Female subject, age 50–59; texture is reported as raised or bumpy and fluid-filled; the patient considered this skin that appeared healthy to them; the patient reports itching; an image taken at a distance; the back of the hand is involved; the condition has been present for less than one week.
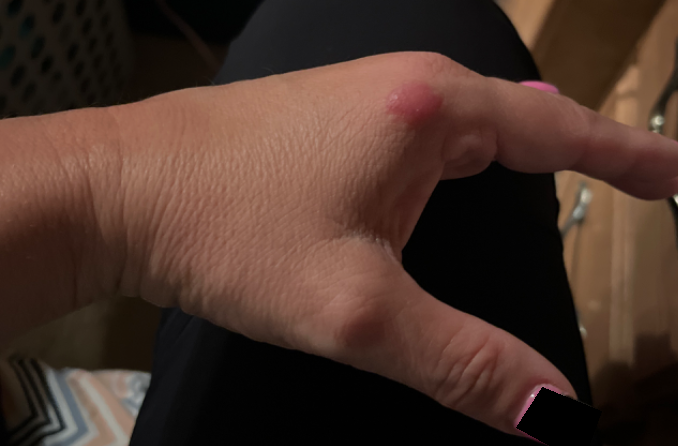assessment: could not be assessed